A dermoscopic close-up of a skin lesion.
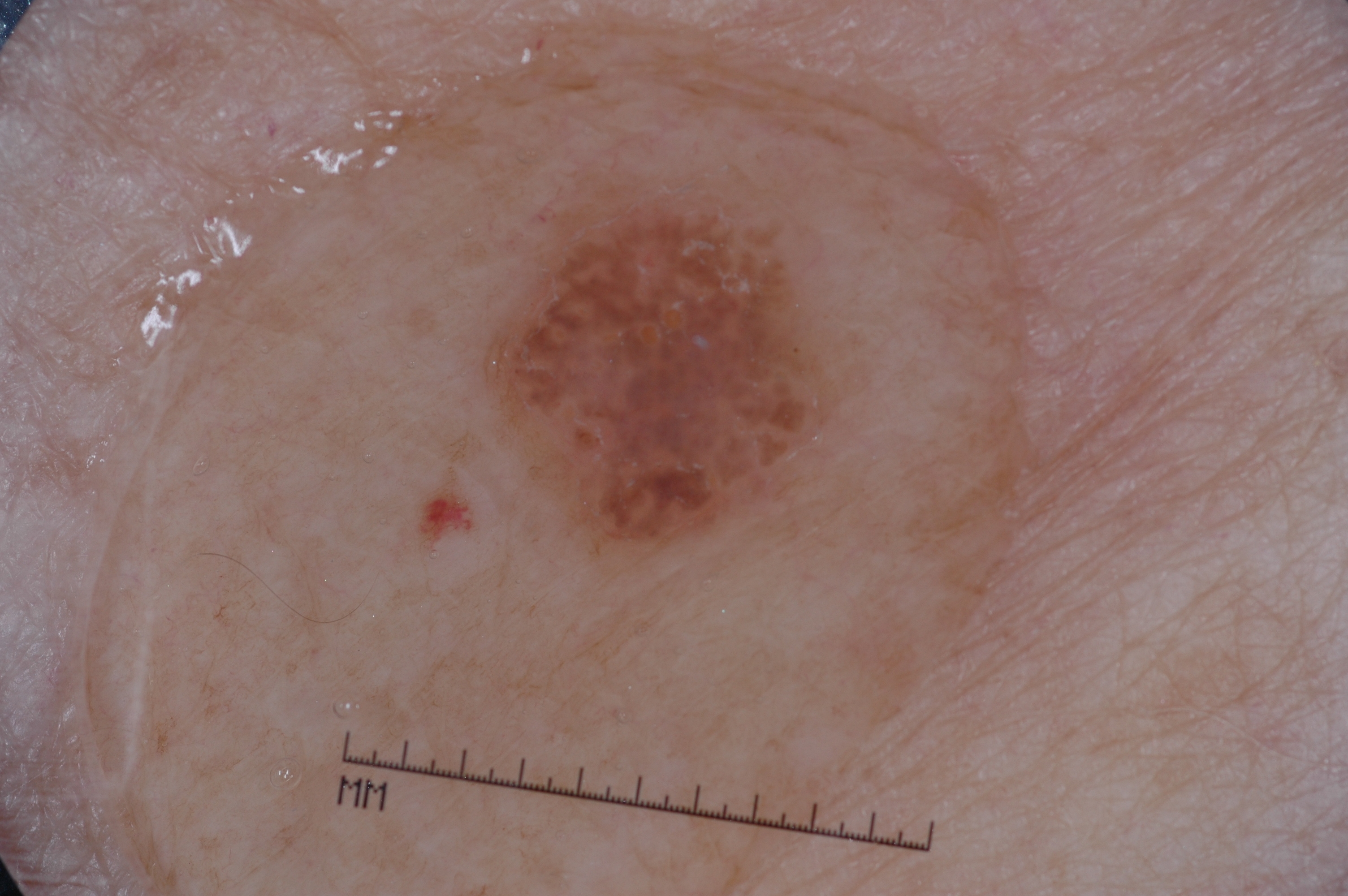Image and clinical context: The lesion spans x1=479 y1=169 x2=842 y2=565. Conclusion: The clinical diagnosis was a seborrheic keratosis, a benign lesion.